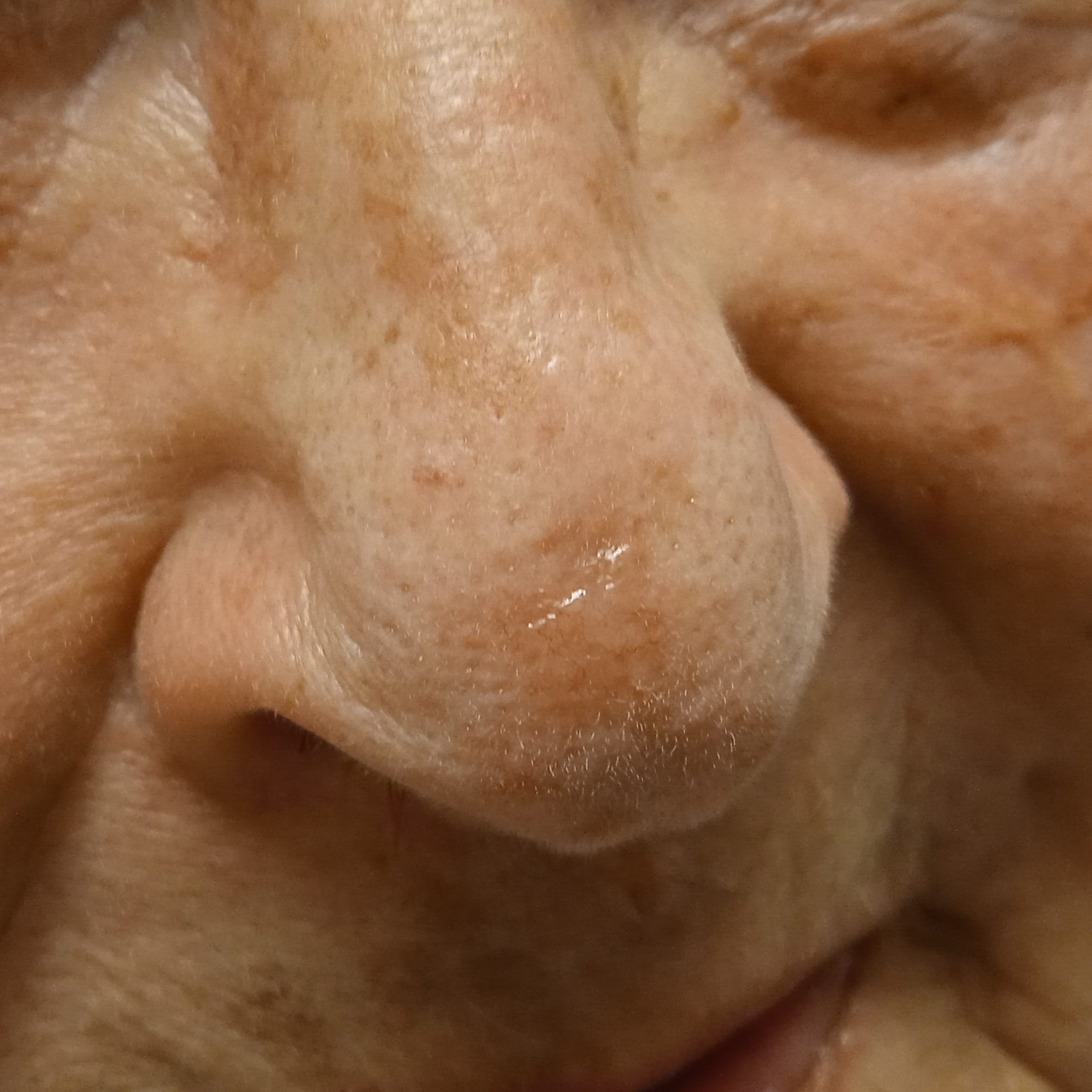Q: What are the relevant risk factors?
A: a personal history of cancer
Q: What is the patient's nevus burden?
A: few melanocytic nevi overall
Q: How does the patient's skin react to sun?
A: skin tans without first burning
Q: Patient demographics?
A: female, 84 years of age
Q: Why was this imaged?
A: clinical suspicion of basal cell carcinoma
Q: Where is the lesion?
A: the face
Q: What did the biopsy show?
A: basal cell carcinoma (biopsy-proven)